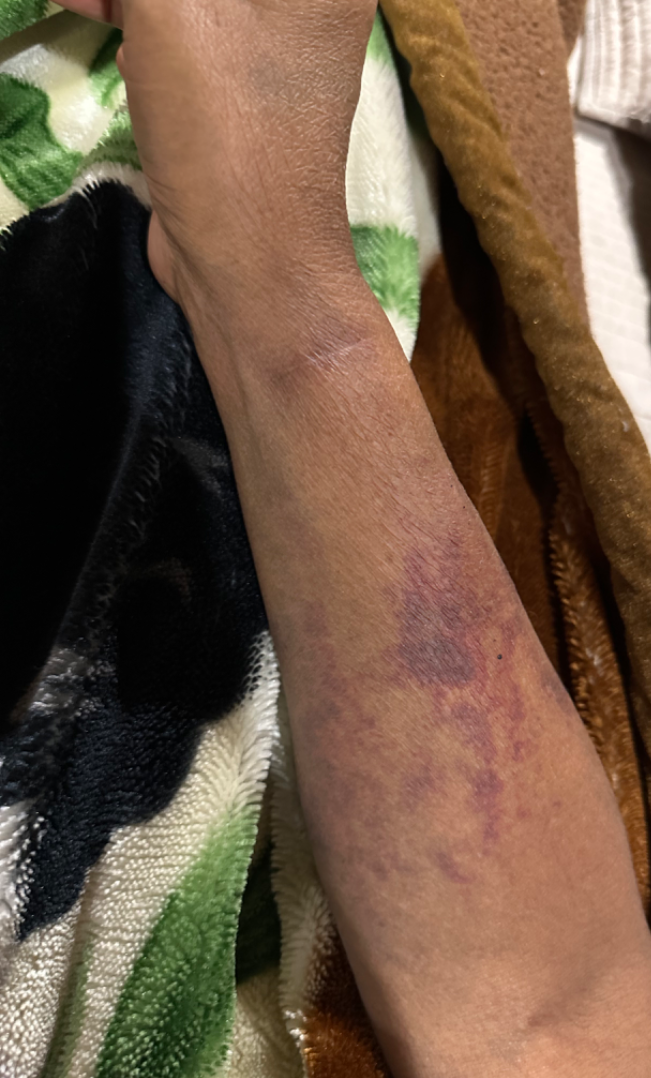The photograph is a close-up of the affected area. The reviewing clinician's impression was: most consistent with Purpura.